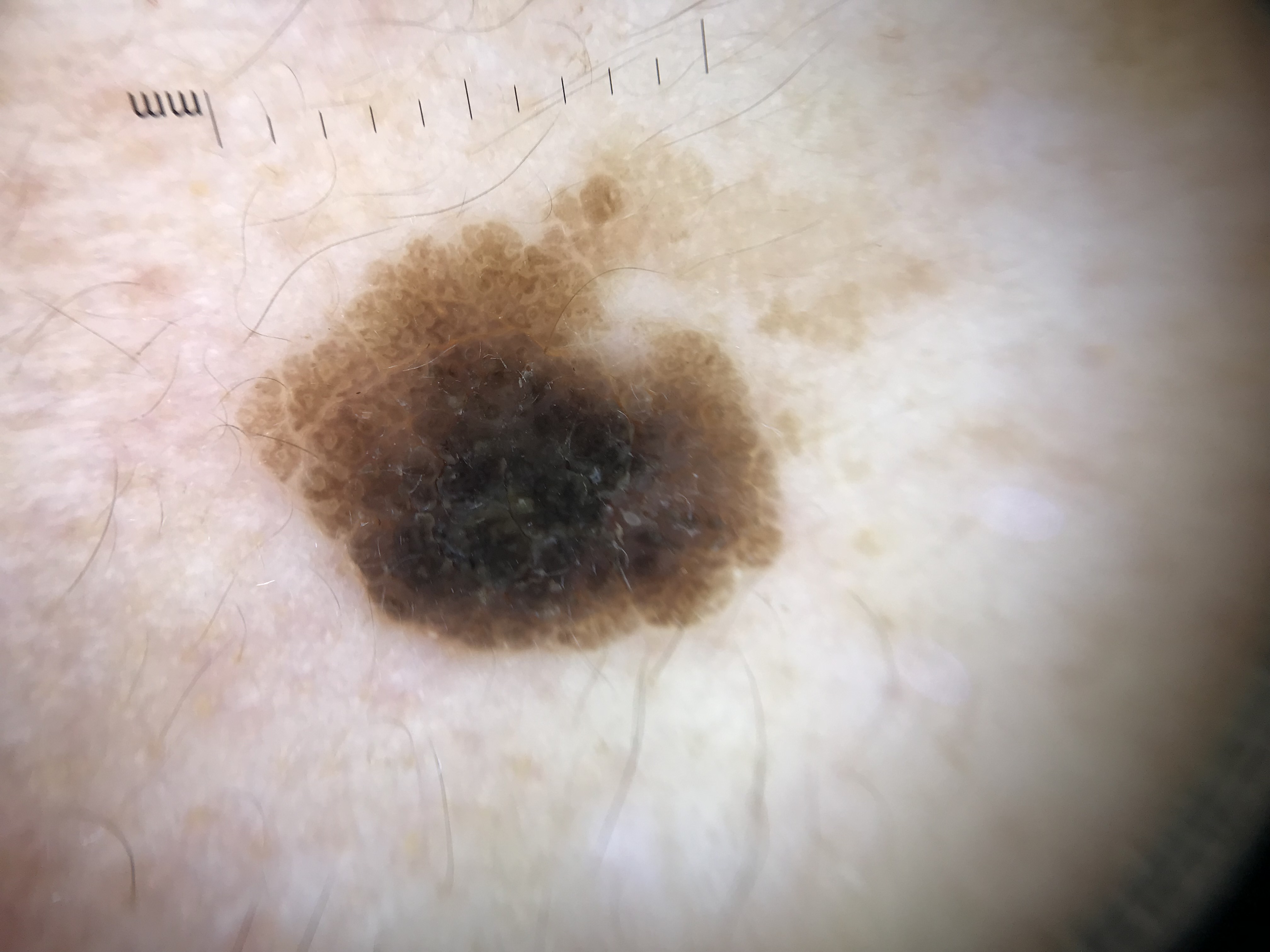Consistent with a seborrheic keratosis.